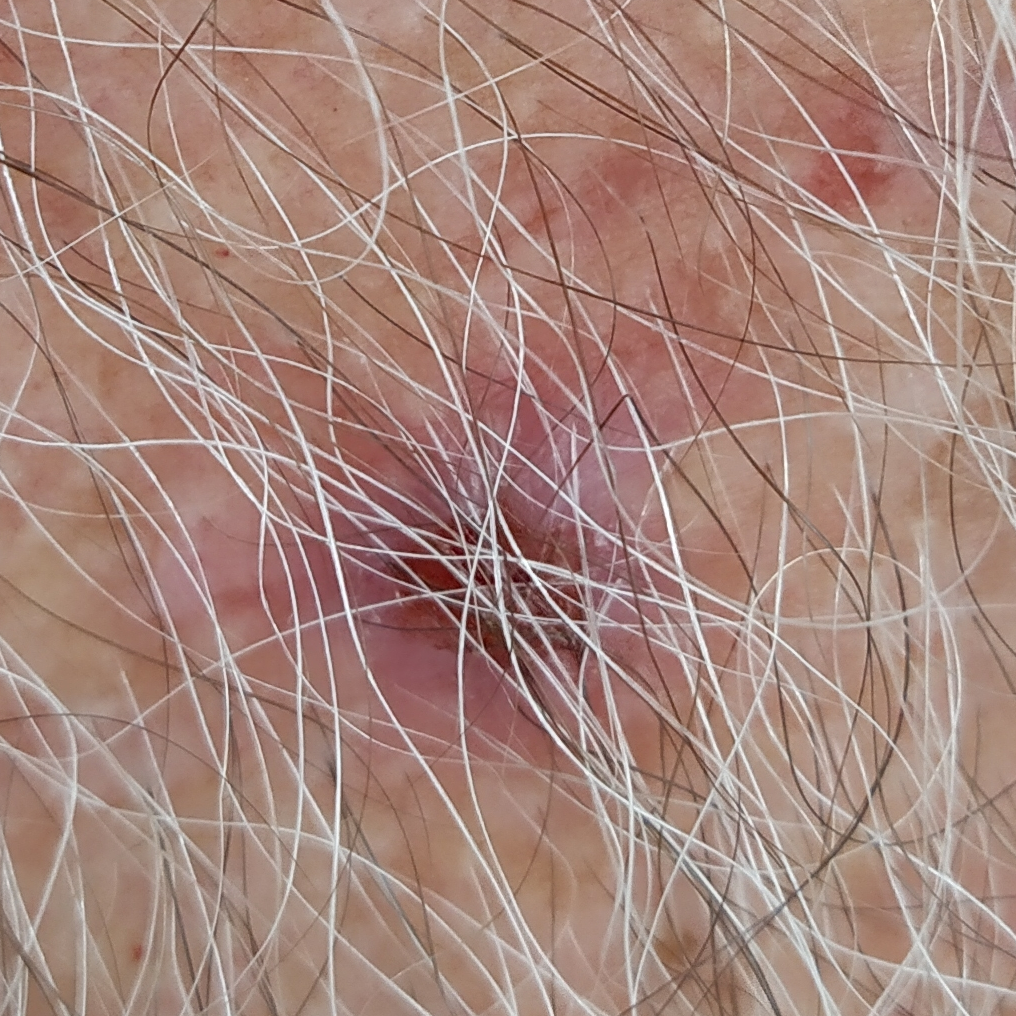– diagnostic label — squamous cell carcinoma (biopsy-proven)